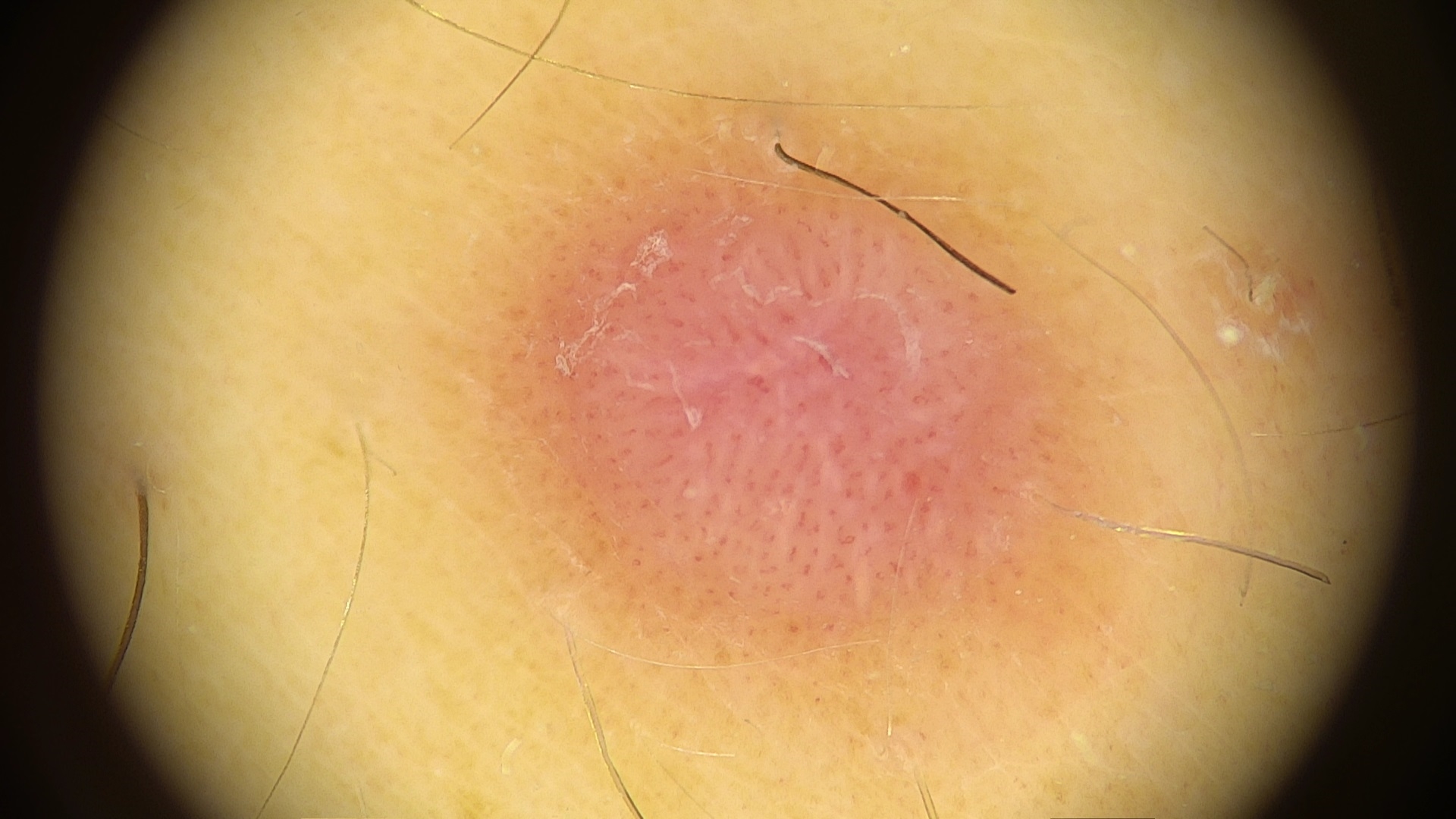Findings:
The morphology is that of a fibro-histiocytic lesion.
Impression:
Consistent with a benign lesion — a dermatofibroma.